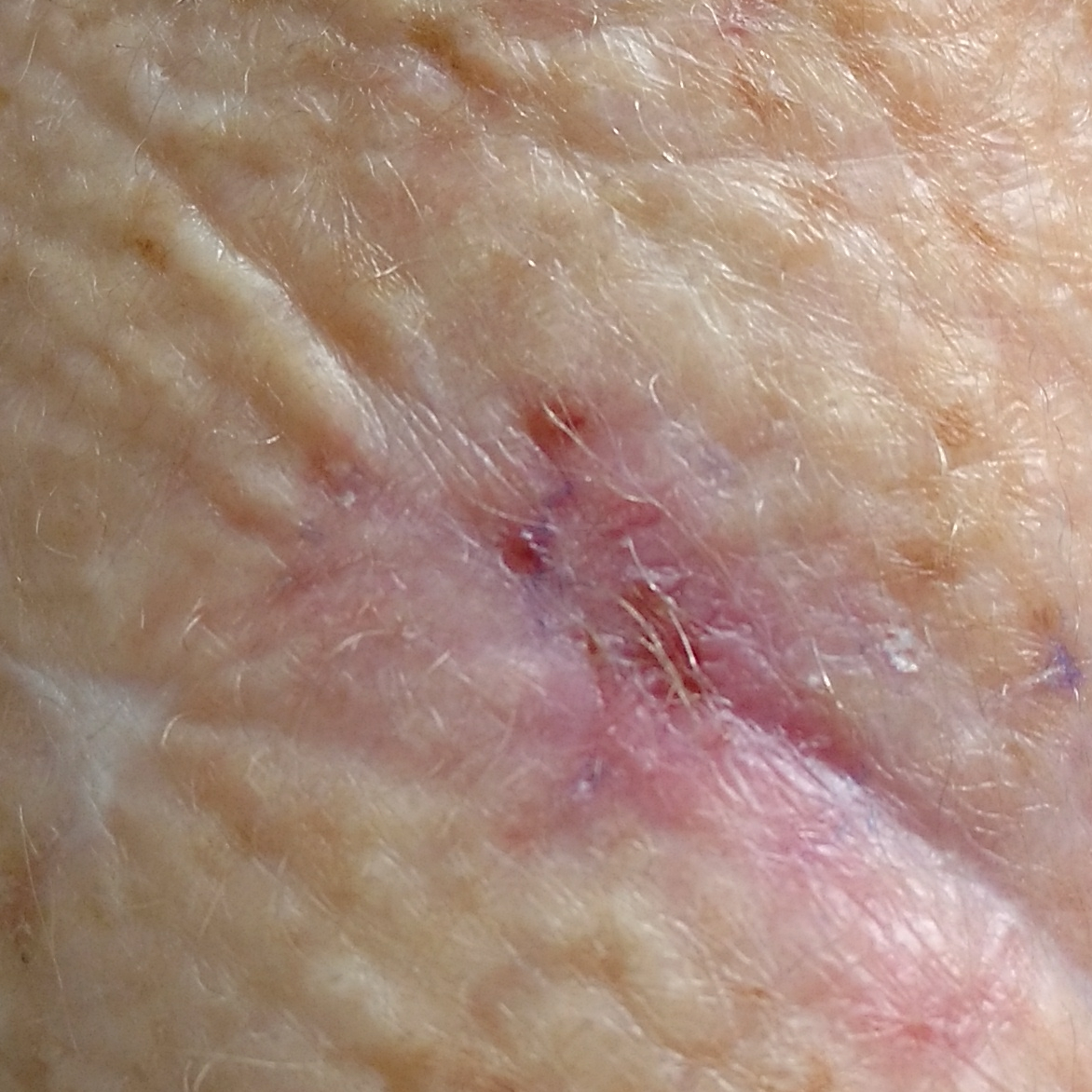The chart notes prior skin cancer (patient or family) and prior malignancy (patient or family). A female patient in their early 70s. The lesion measures 15 × 8 mm. The patient describes that the lesion hurts, has bled, itches, and has grown, but has not changed and is not elevated. Histopathology confirmed a basal cell carcinoma.